A dermoscopic close-up of a skin lesion: 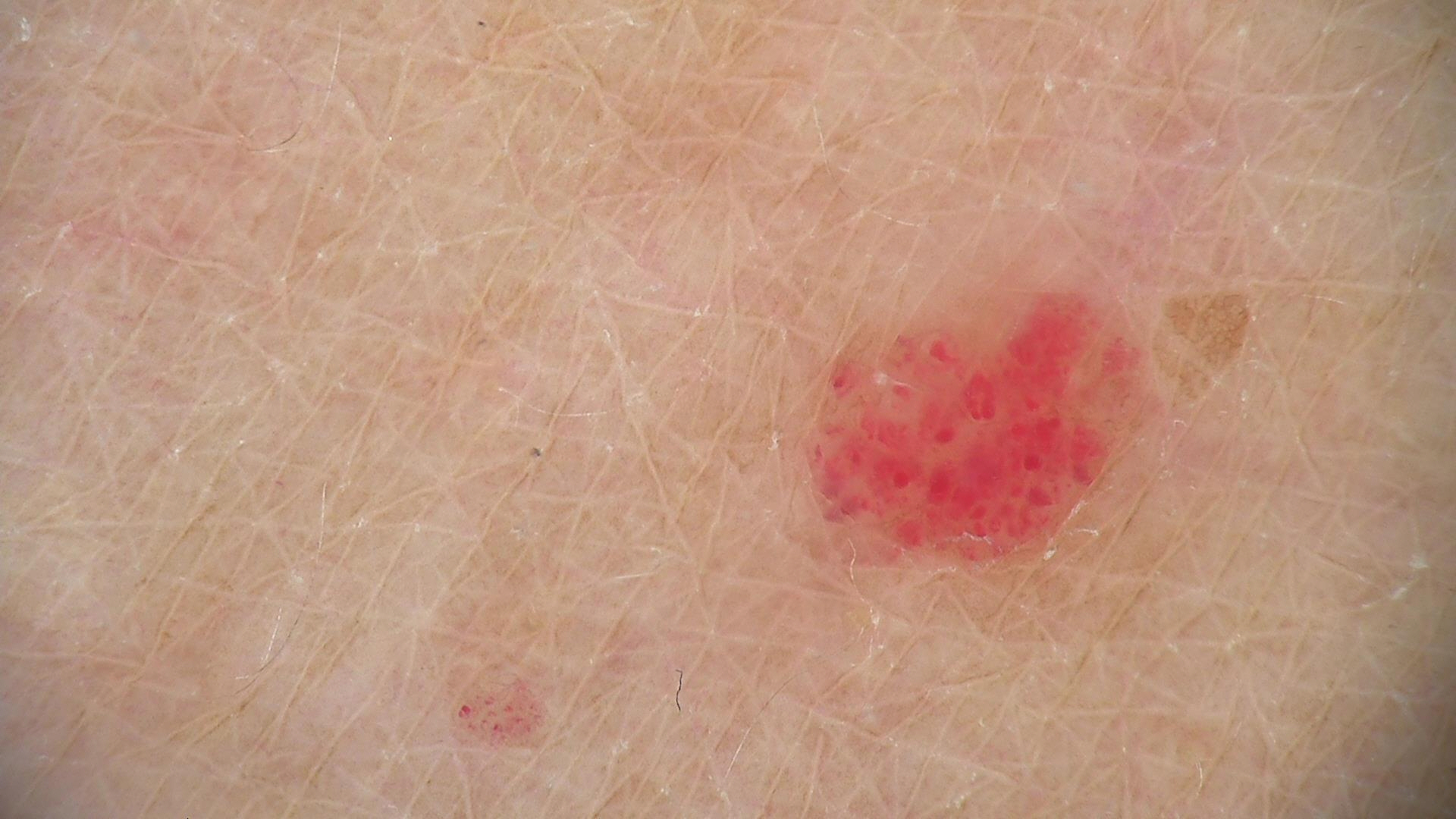subtype: vascular
diagnostic label: hemangioma (expert consensus)